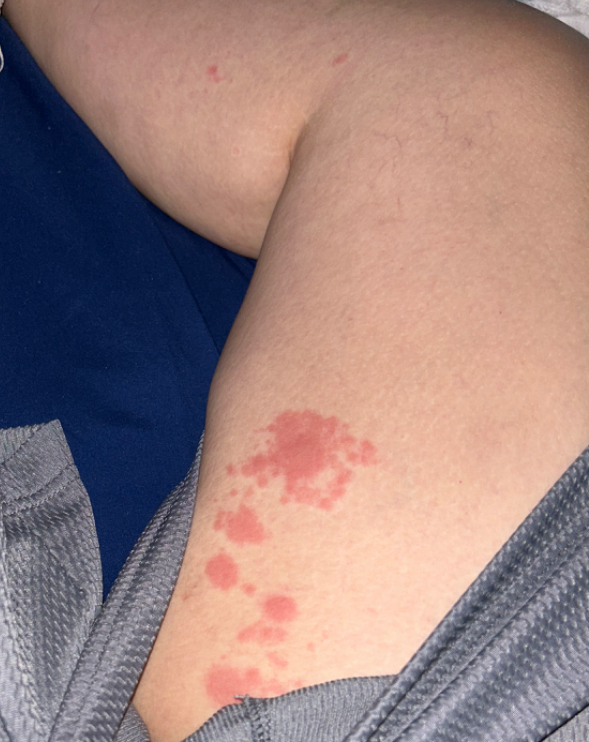photo taken = at an angle
dermatologist impression = a single dermatologist reviewed the case: most consistent with Tinea; also consider Candidal intertrigo; the differential also includes Erythema multiforme